The contributor is male; the leg is involved; the patient also reports joint pain and fatigue; the lesion is described as raised or bumpy; the condition has been present for about one day; no relevant lesion symptoms reported; an image taken at an angle:
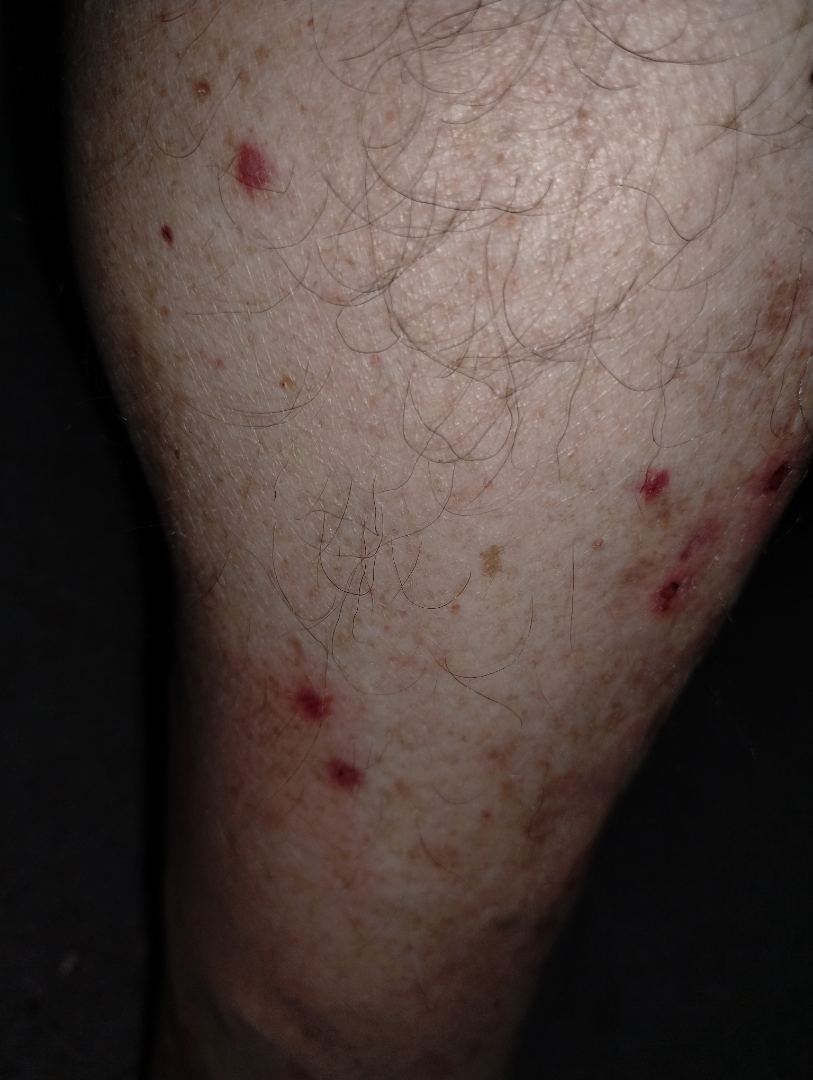Q: What conditions are considered?
A: Purpura (possible); Folliculitis (possible); Pseudolymphoma (unlikely); Insect Bite (unlikely)